A dermoscopic close-up of a skin lesion.
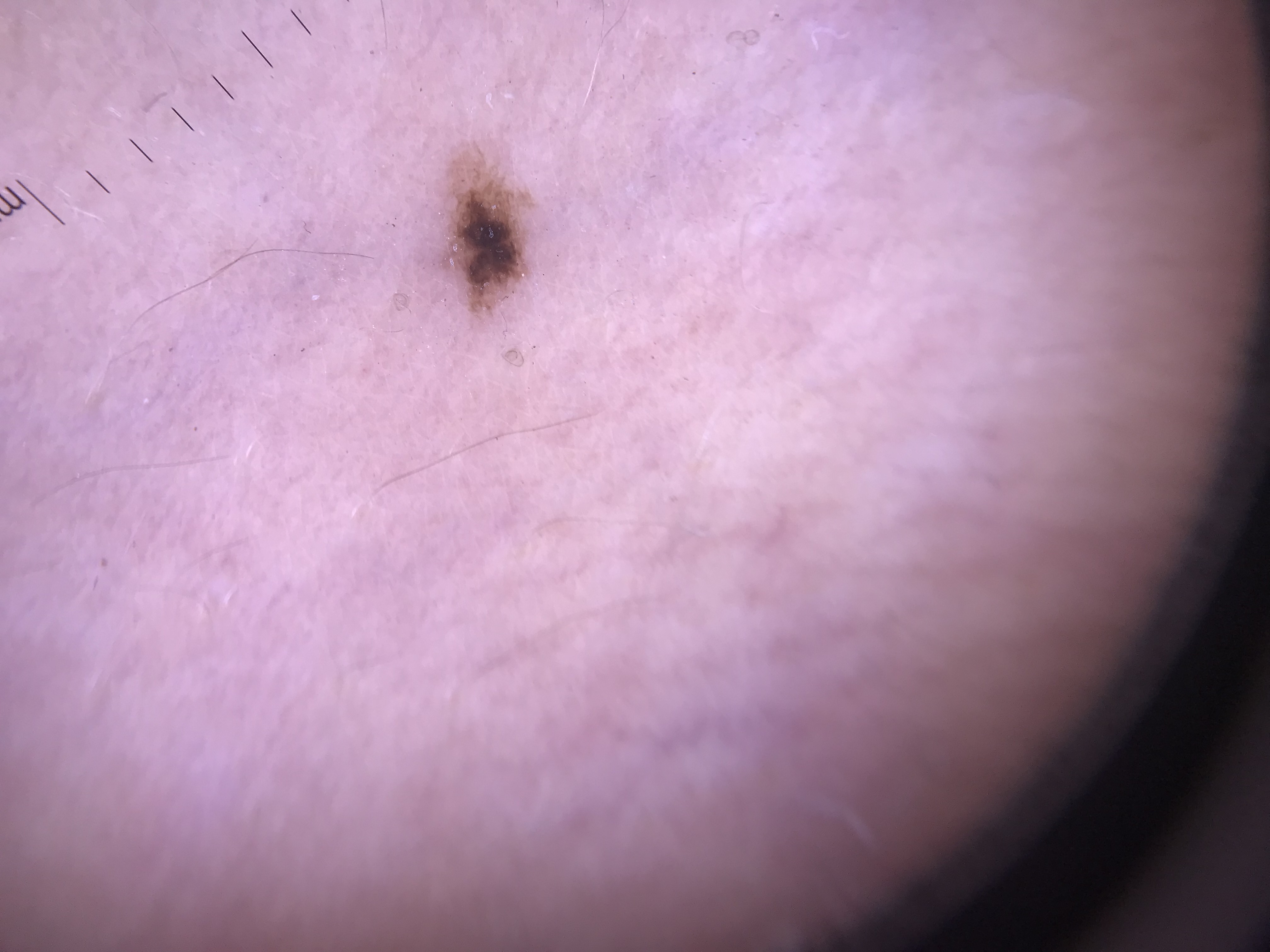label: dysplastic junctional nevus (expert consensus).